The lesion involves the back of the hand. The photo was captured at an angle:
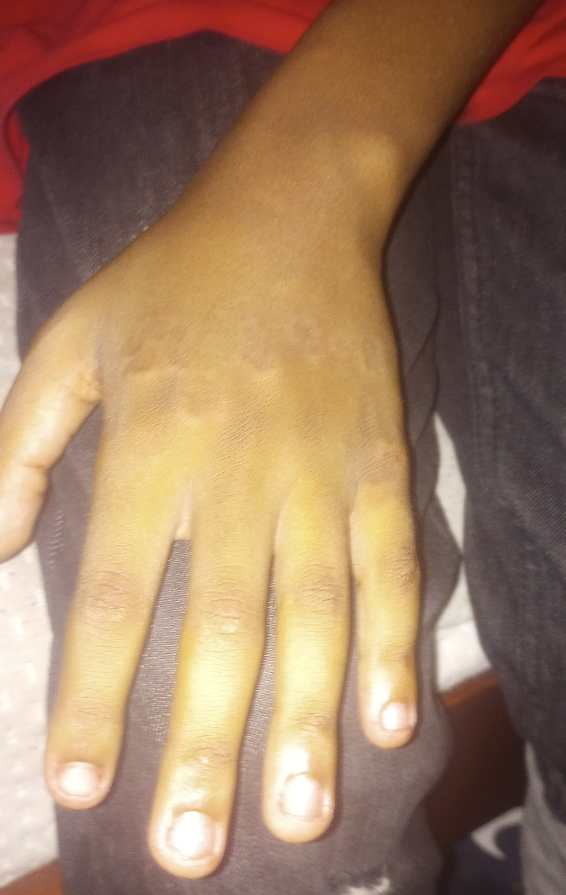assessment: not assessable
patient describes the issue as: a pigmentary problem
surface texture: raised or bumpy
constitutional symptoms: none reported